The leg is involved; close-up view:
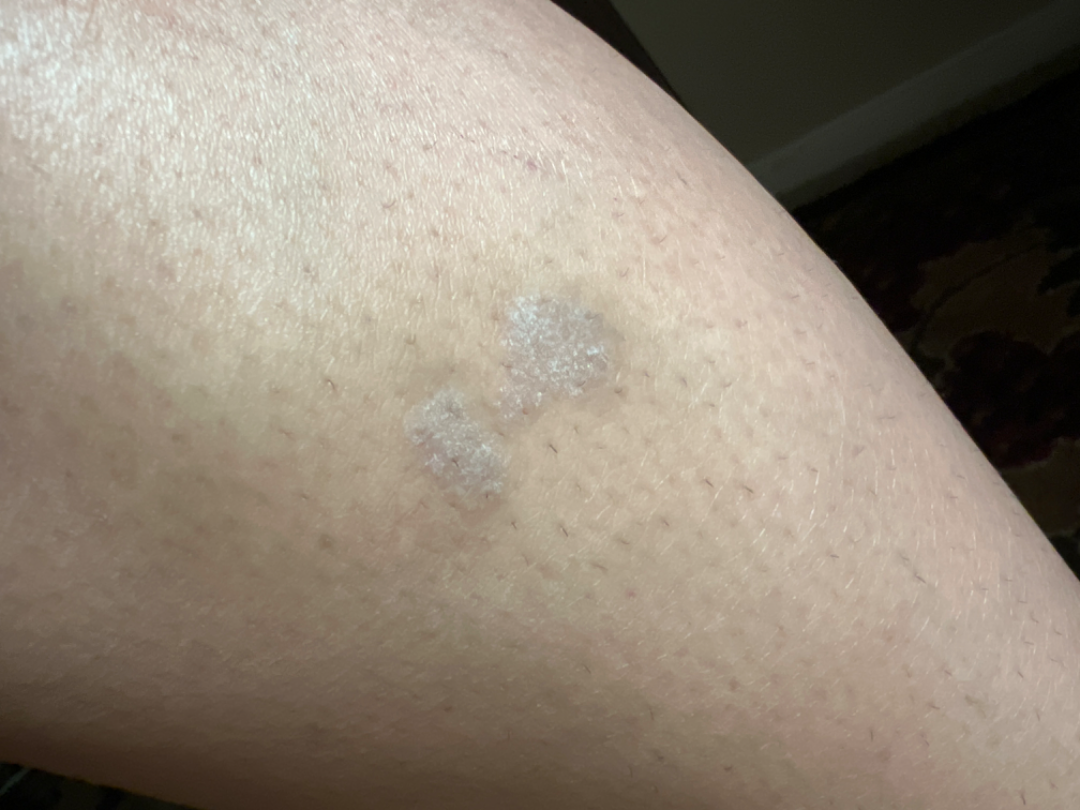The contributor reports the condition has been present for more than five years. The contributor reports the lesion is flat and rough or flaky. Consistent with Lichen planus/lichenoid eruption.